An image taken at an angle; the leg is involved; the subject is 30–39, female — 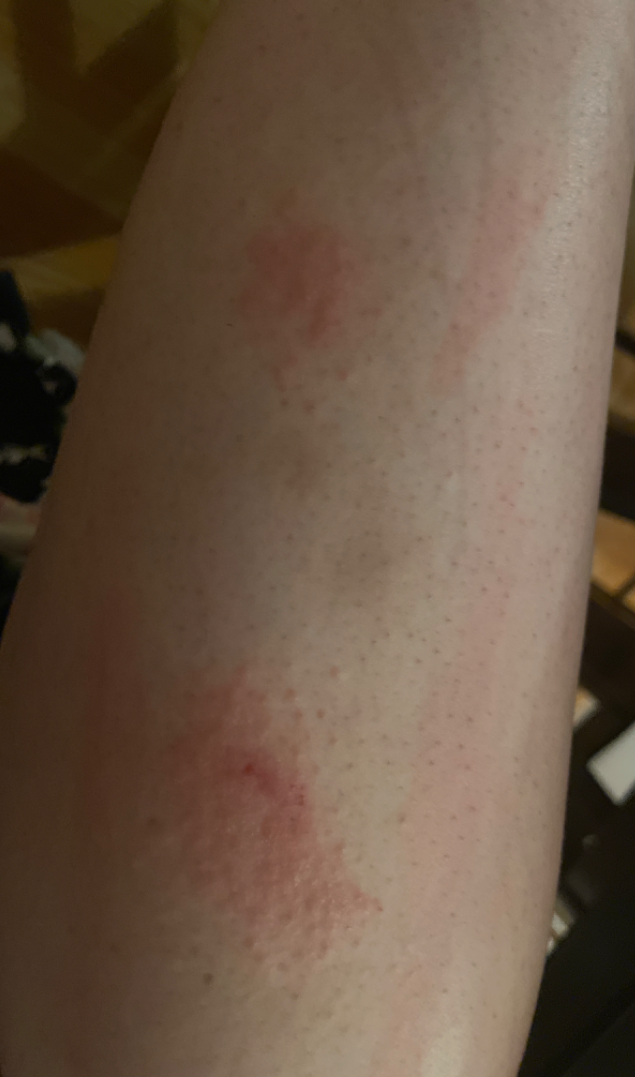assessment = ungradable on photographic review